A dermoscopy image of a single skin lesion.
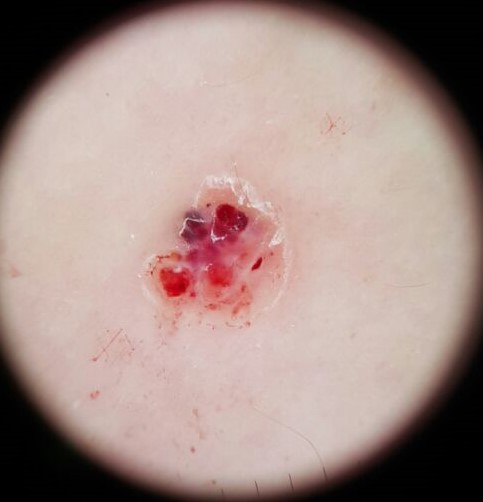This is a vascular lesion.
Consistent with a benign lesion — an angiokeratoma.